A dermatoscopic image of a skin lesion:
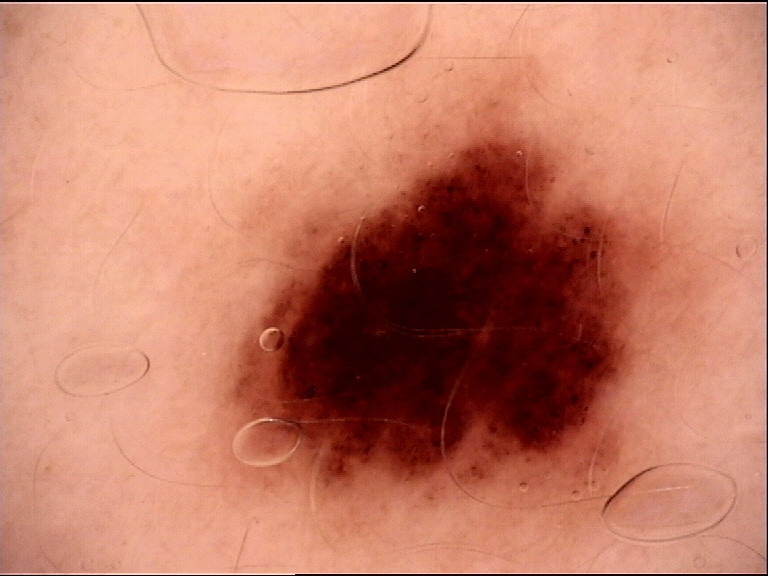{
  "diagnosis": {
    "name": "dysplastic compound nevus",
    "code": "cd",
    "malignancy": "benign",
    "super_class": "melanocytic",
    "confirmation": "expert consensus"
  }
}